A skin lesion imaged with a dermatoscope.
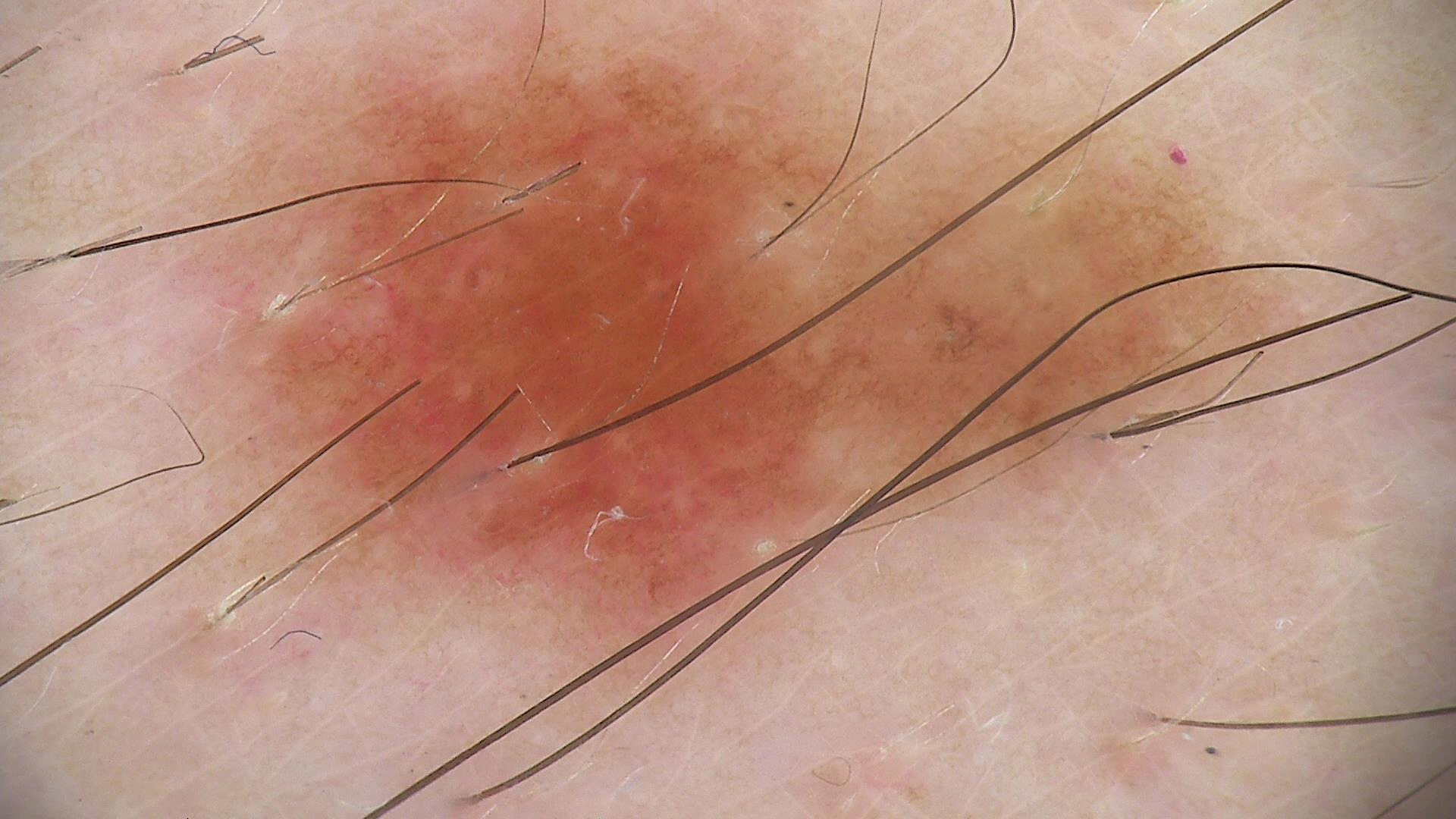<dermoscopy>
<diagnosis>
<name>dysplastic junctional nevus</name>
<code>jd</code>
<malignancy>benign</malignancy>
<super_class>melanocytic</super_class>
<confirmation>expert consensus</confirmation>
</diagnosis>
</dermoscopy>